A skin lesion imaged with a dermatoscope.
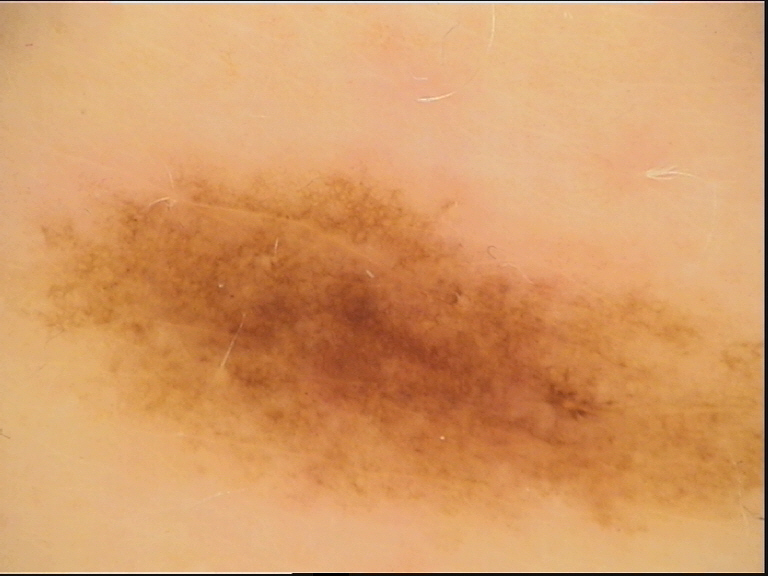{"diagnosis": {"name": "dysplastic junctional nevus", "code": "jd", "malignancy": "benign", "super_class": "melanocytic", "confirmation": "expert consensus"}}